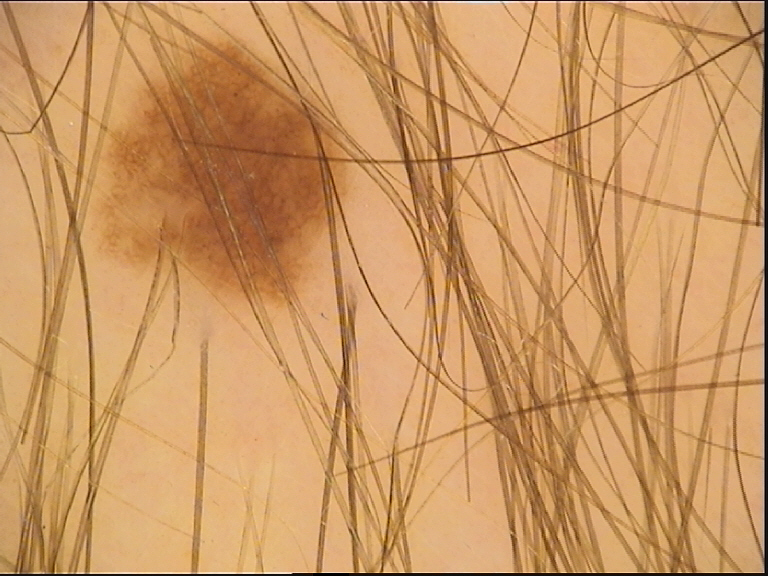Summary:
A skin lesion imaged with a dermatoscope.
Impression:
Labeled as a benign lesion — a dysplastic junctional nevus.